A subject in their 70s; a clinical close-up photograph of a skin lesion: 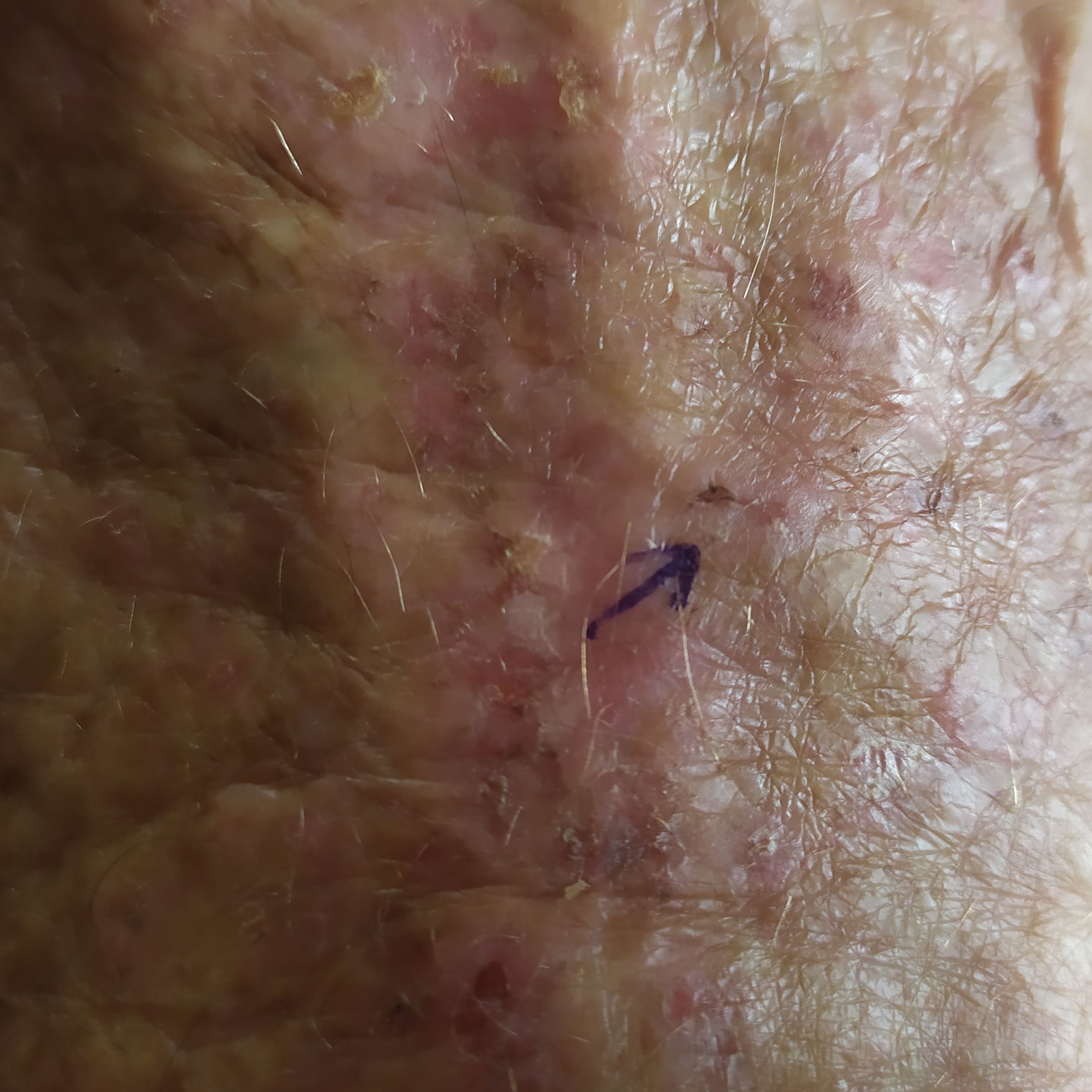Located on a hand.
The patient reports that the lesion has not grown and has not bled.
Clinically diagnosed as a lesion with uncertain malignant potential — an actinic keratosis.